A smartphone photograph of a skin lesion · a female subject in their late 60s — 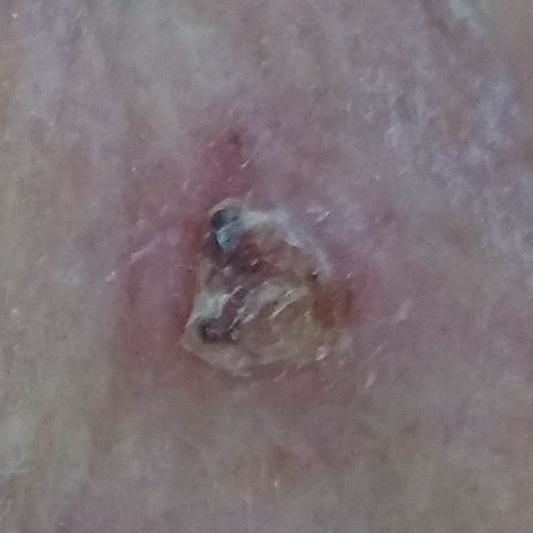Patient and lesion: The lesion was found on the face. By the patient's account, the lesion has bled, hurts, itches, has grown, and is elevated, but has not changed. Conclusion: Confirmed on histopathology as a basal cell carcinoma.